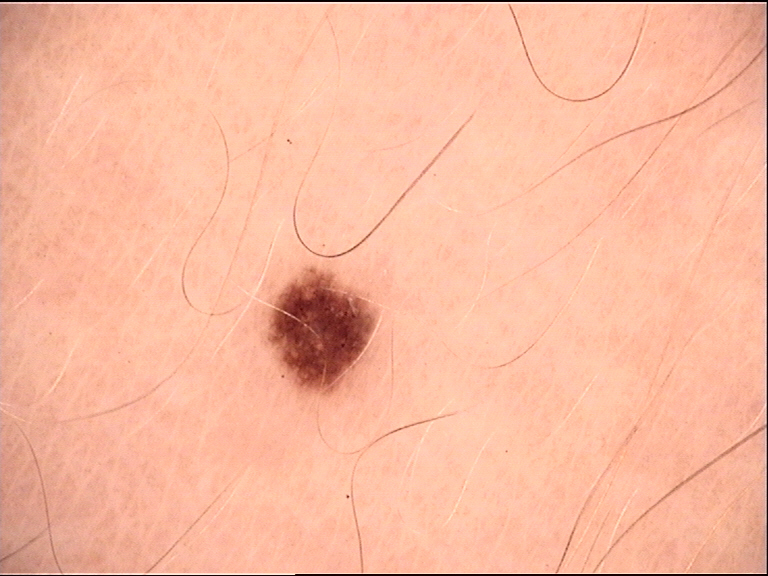Impression: The diagnosis was a dysplastic junctional nevus.